A clinical photograph of a skin lesion · a patient in their early 60s.
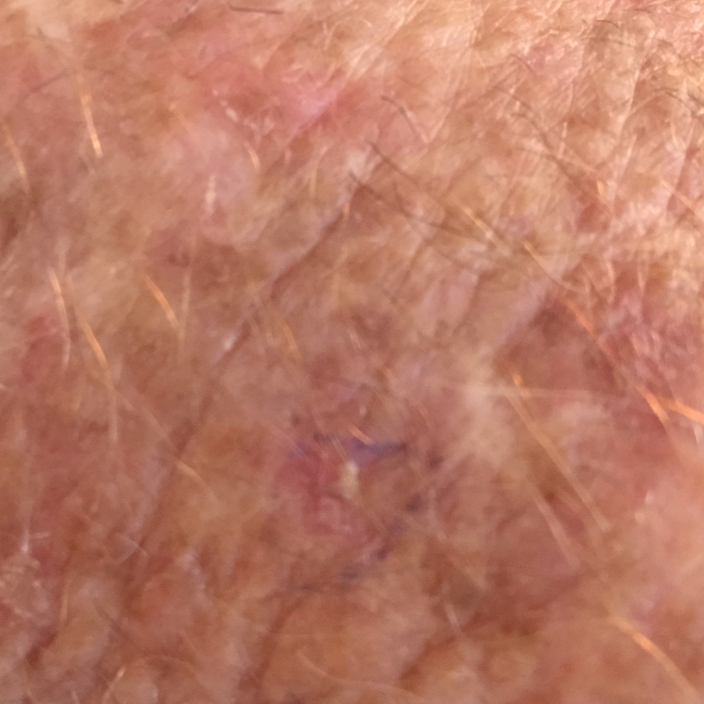{"lesion_location": "a forearm", "symptoms": {"present": ["itching"], "absent": ["bleeding", "growth"]}, "diagnosis": {"name": "actinic keratosis", "code": "ACK", "malignancy": "indeterminate", "confirmation": "clinical consensus"}}